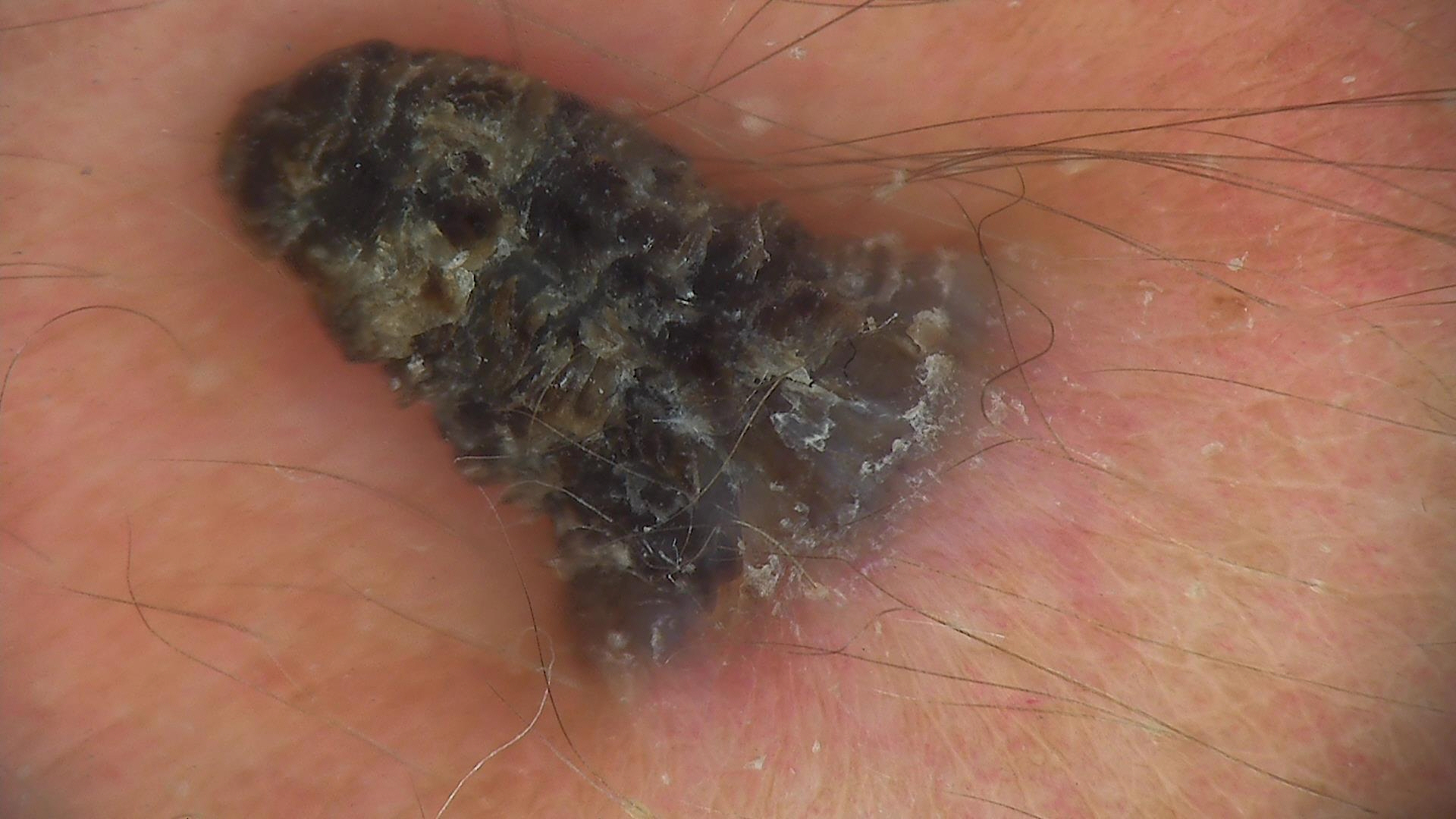pathology: cutaneous horn (biopsy-proven)